The photograph is a close-up of the affected area.
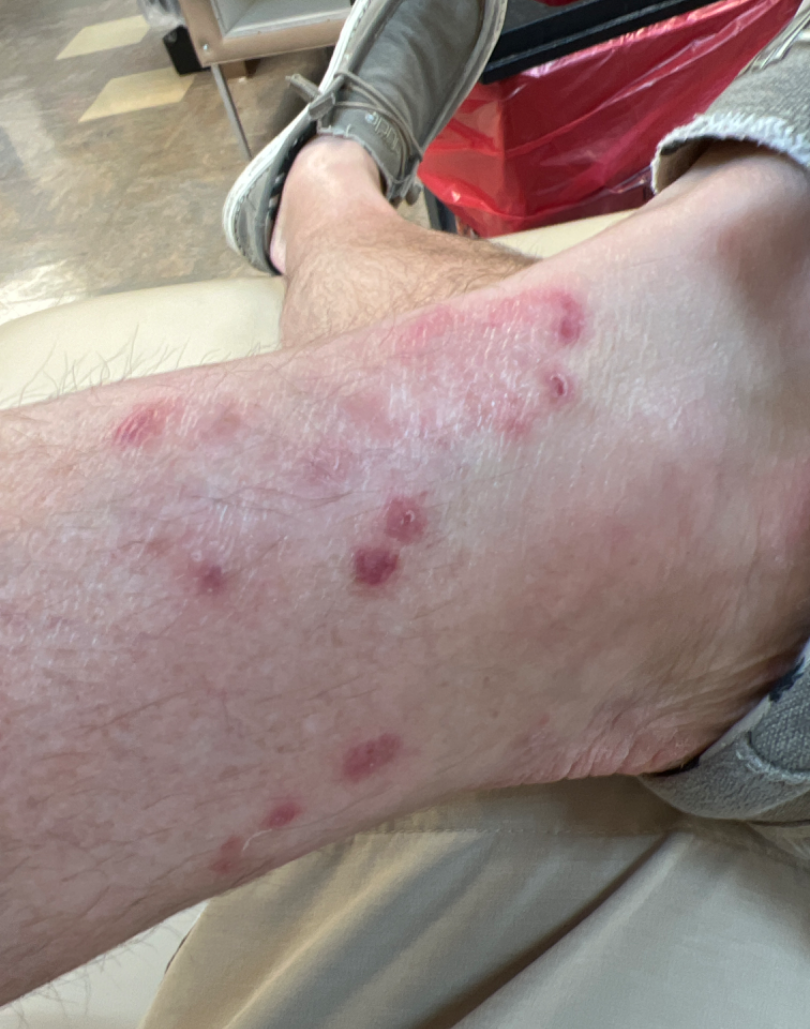differential diagnosis: Tinea (favored); Granuloma annulare (considered); Eczema (considered).